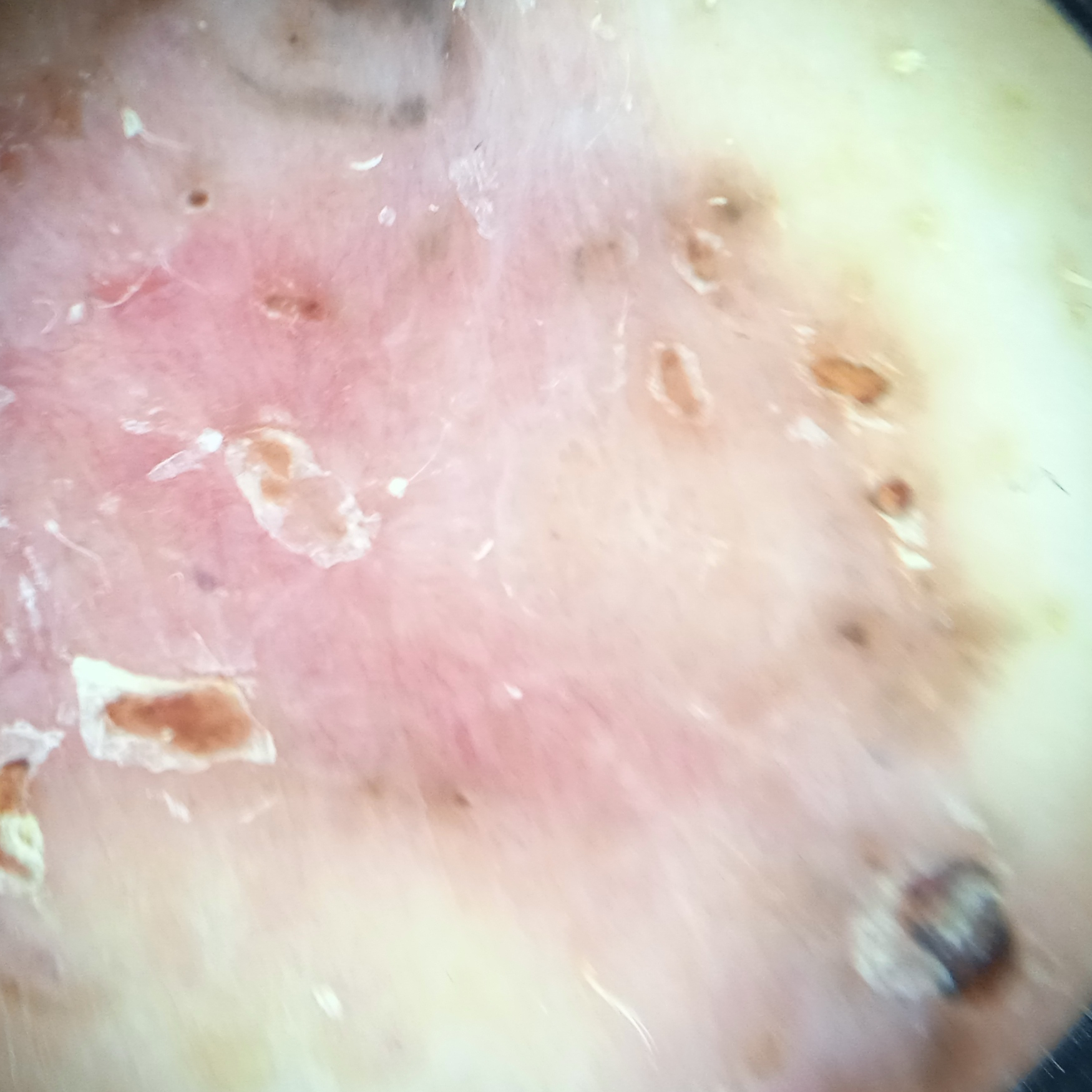risk_factors:
  positive:
    - a personal history of cancer
  negative:
    - no prior organ transplant
    - no sunbed use
sun_reaction: skin tans without first burning
image: dermoscopy
referral: clinical suspicion of basal cell carcinoma
mole_burden: a moderate number of melanocytic nevi
lesion_location: the torso
lesion_size:
  diameter_mm: 66.0
diagnosis:
  name: basal cell carcinoma
  malignancy: malignant
  procedure: punch biopsy
  tumor_thickness_mm: 0.3